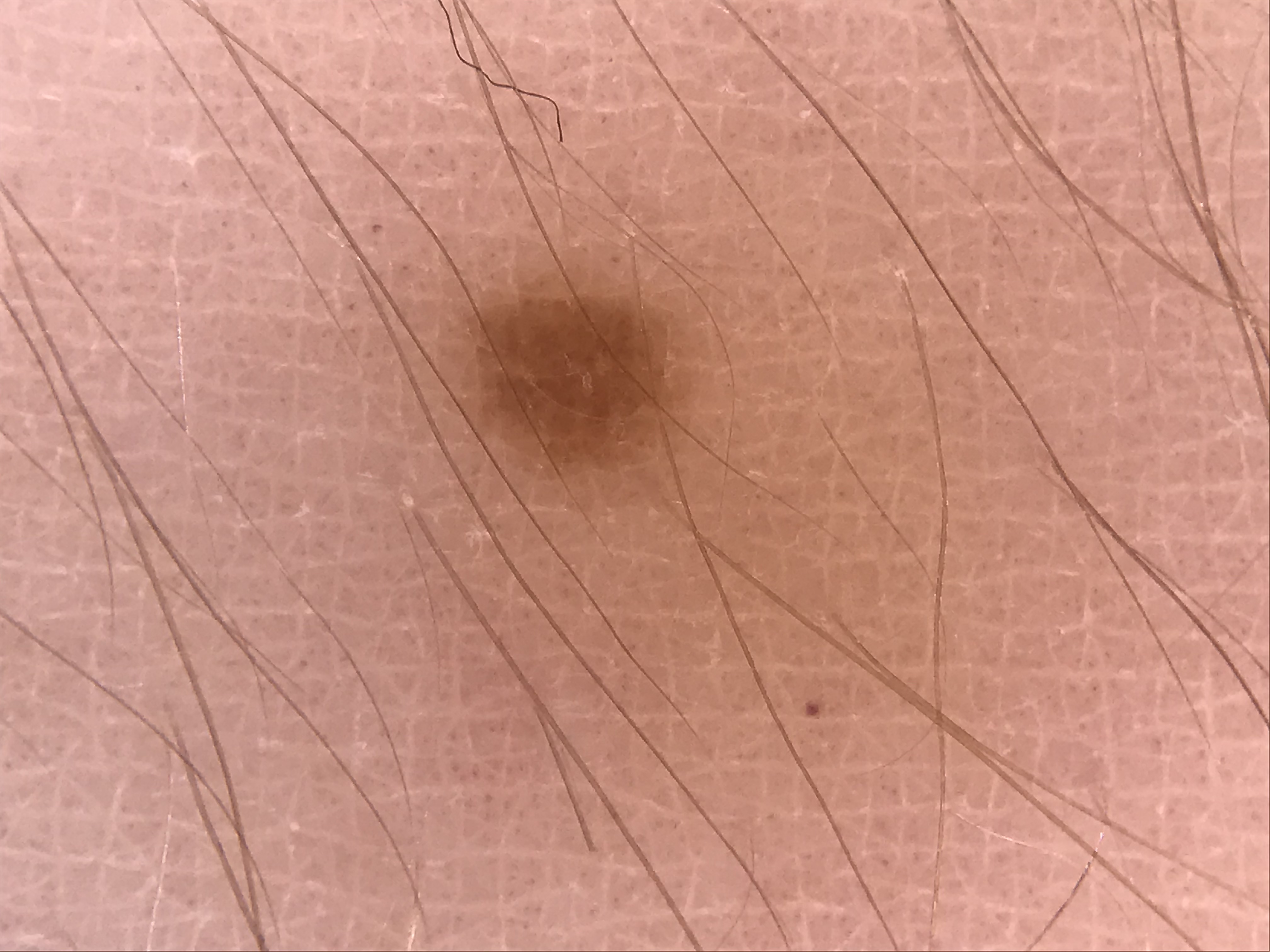The diagnostic label was a junctional nevus.